Located on the front of the torso, head or neck, leg and back of the torso. The photograph was taken at an angle — 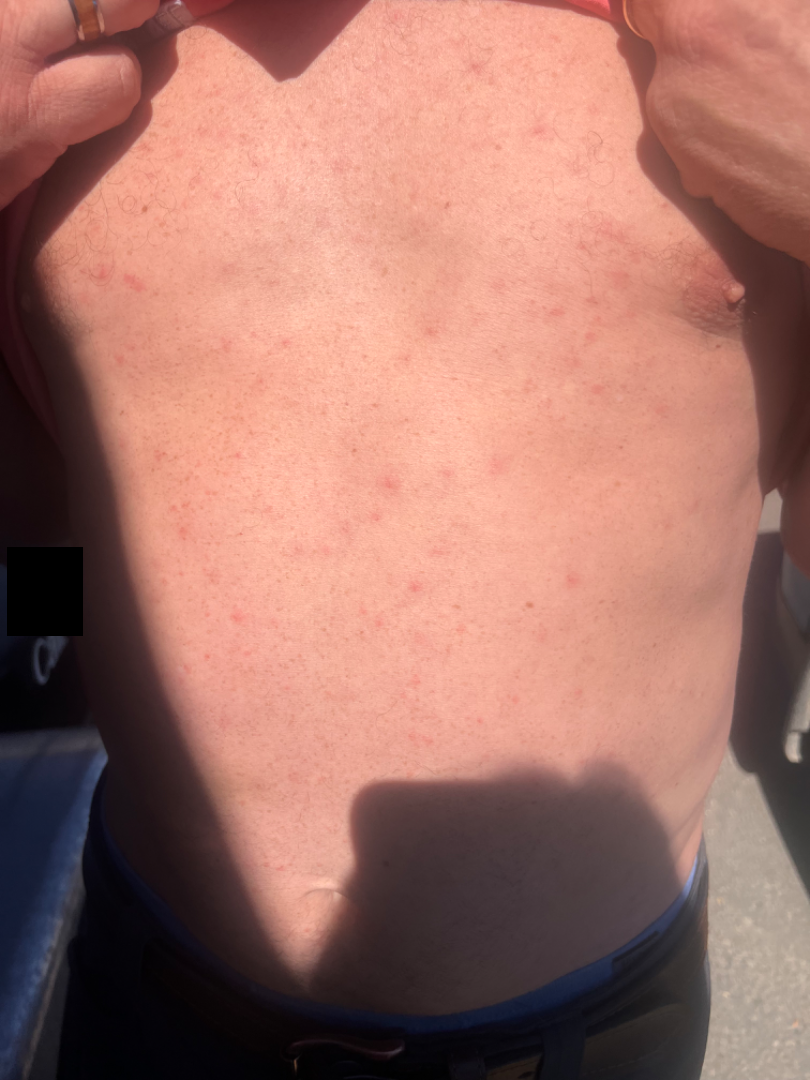The reviewer was unable to grade this case for skin condition.